A dermoscopic photograph of a skin lesion.
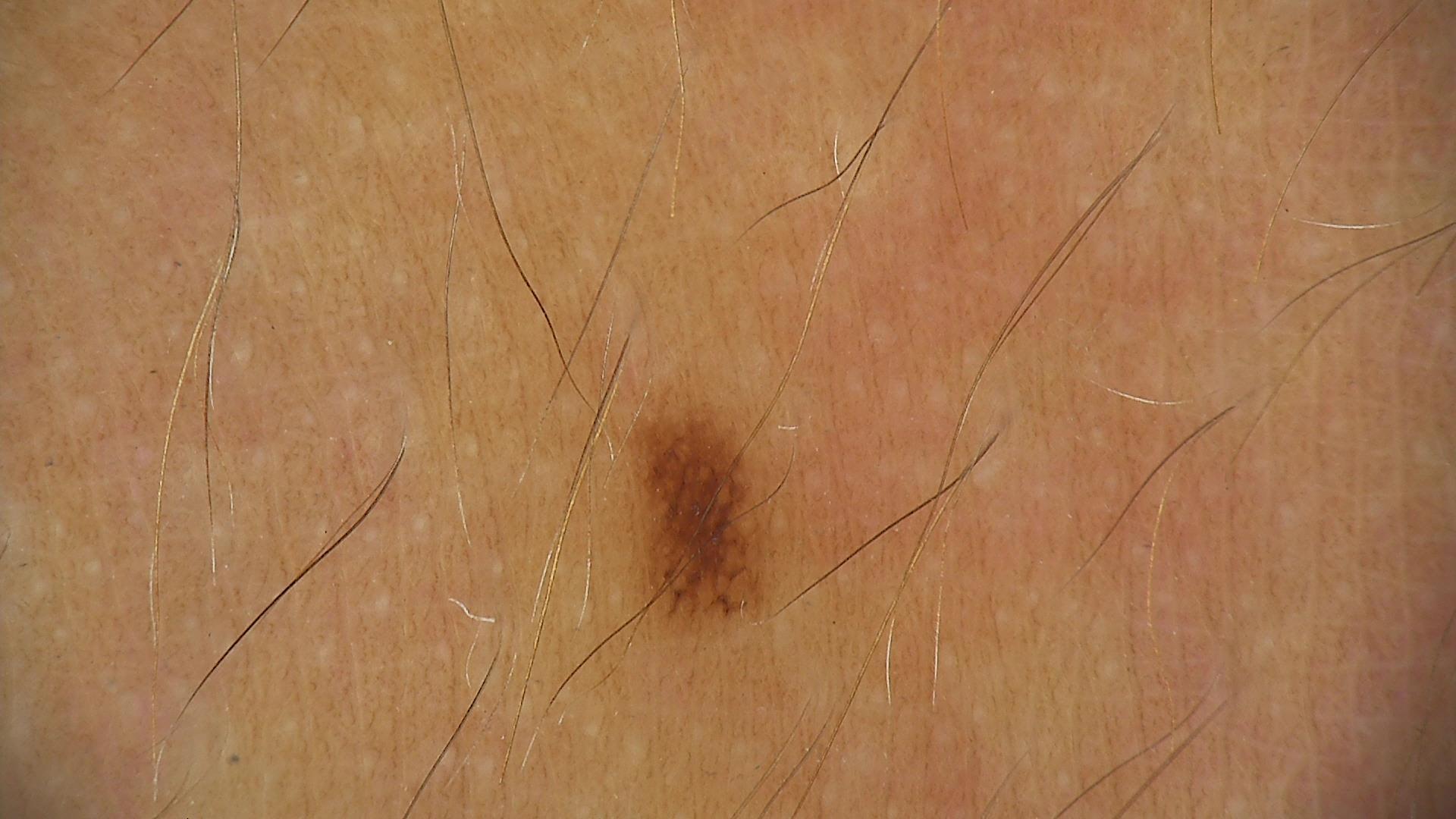| key | value |
|---|---|
| label | dysplastic junctional nevus (expert consensus) |